This is a close-up image: 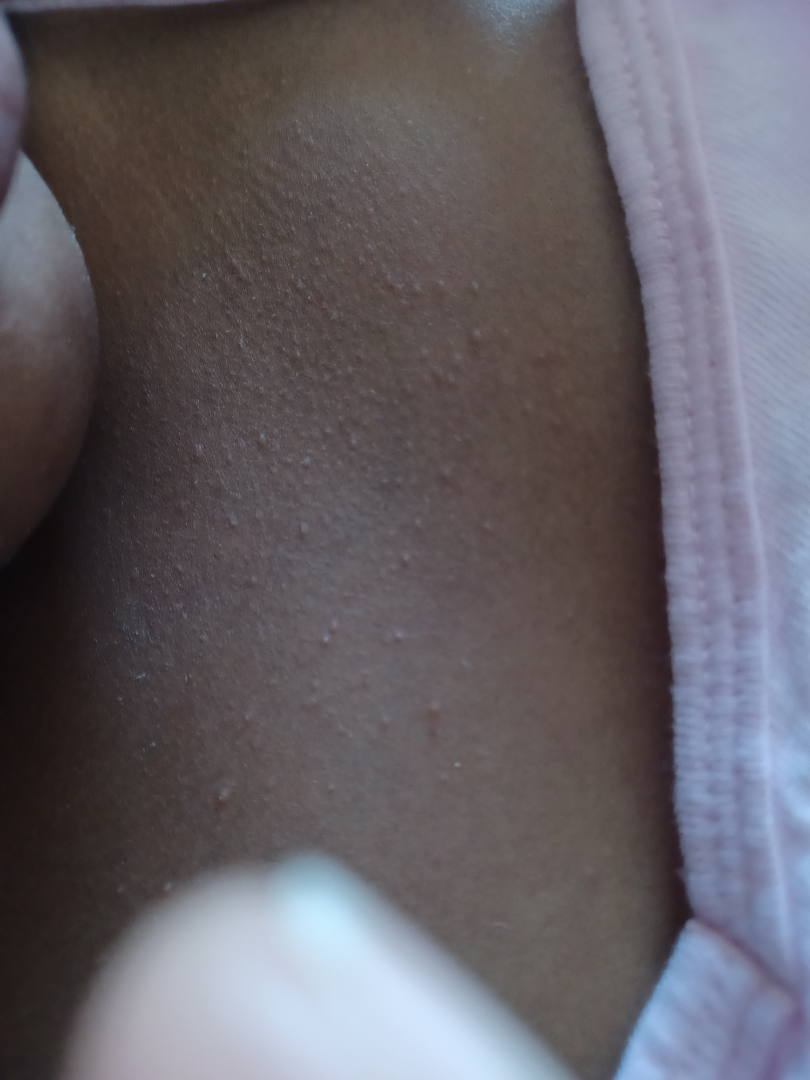– differential — single-reviewer assessment: in keeping with Eczema